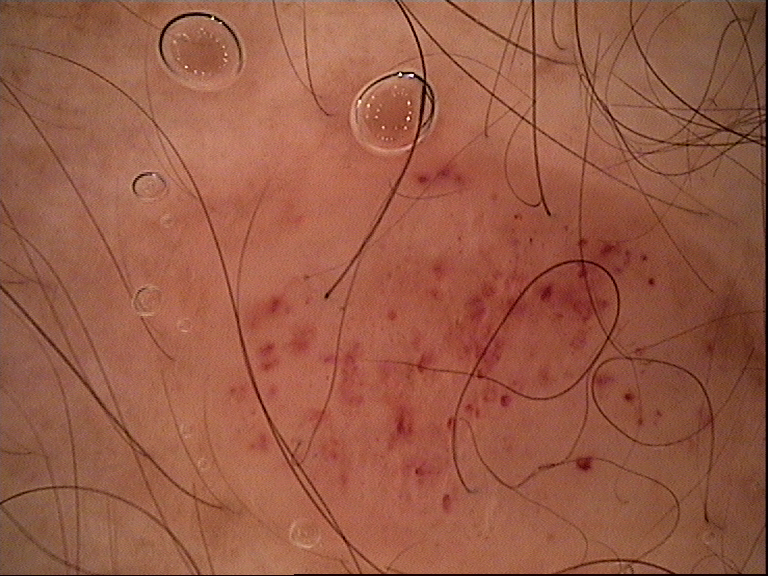class: hemangioma (expert consensus).